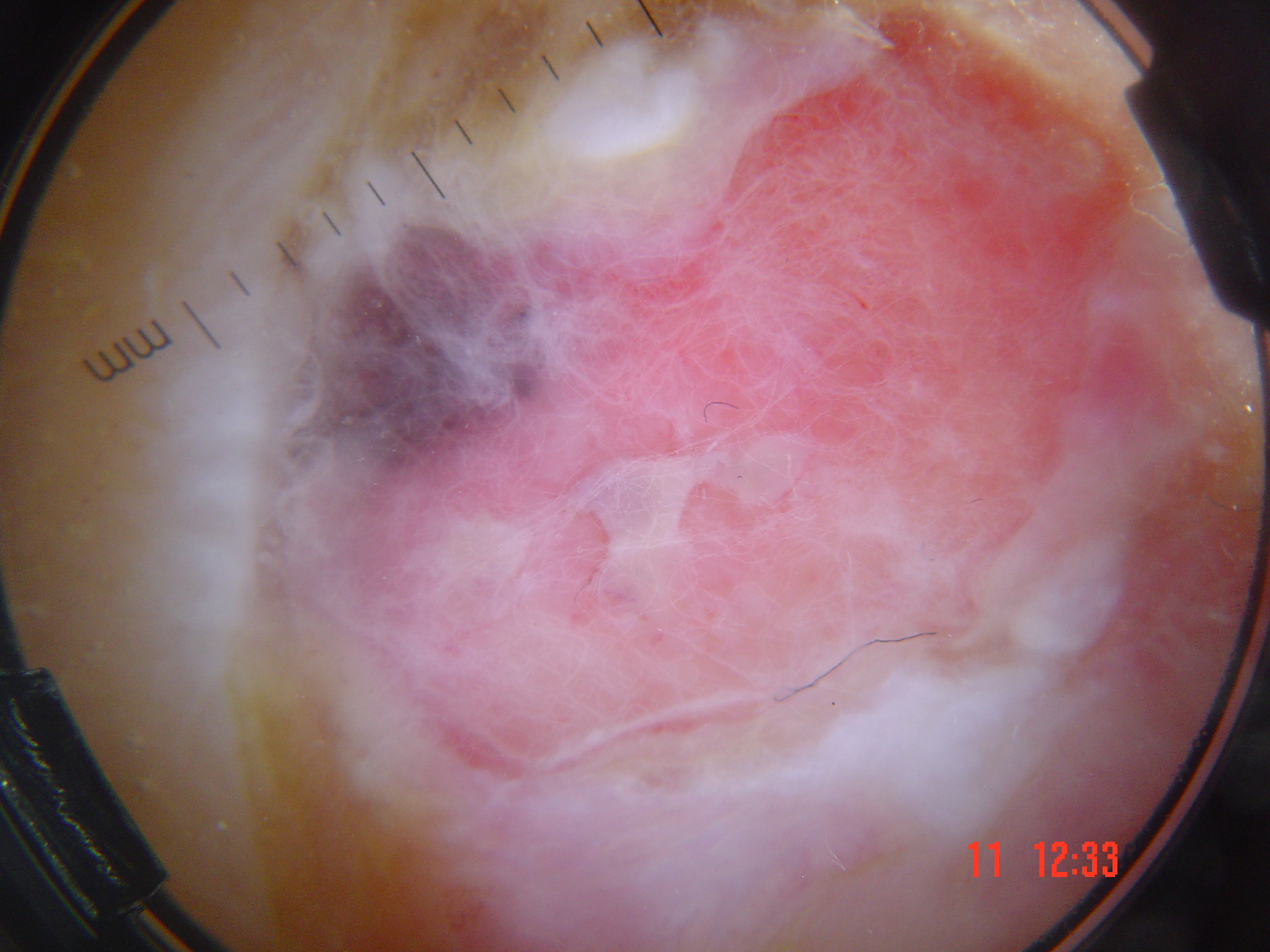Q: What kind of image is this?
A: dermatoscopy
Q: What is the diagnosis?
A: acral nodular melanoma (biopsy-proven)